A dermoscopic image of a skin lesion.
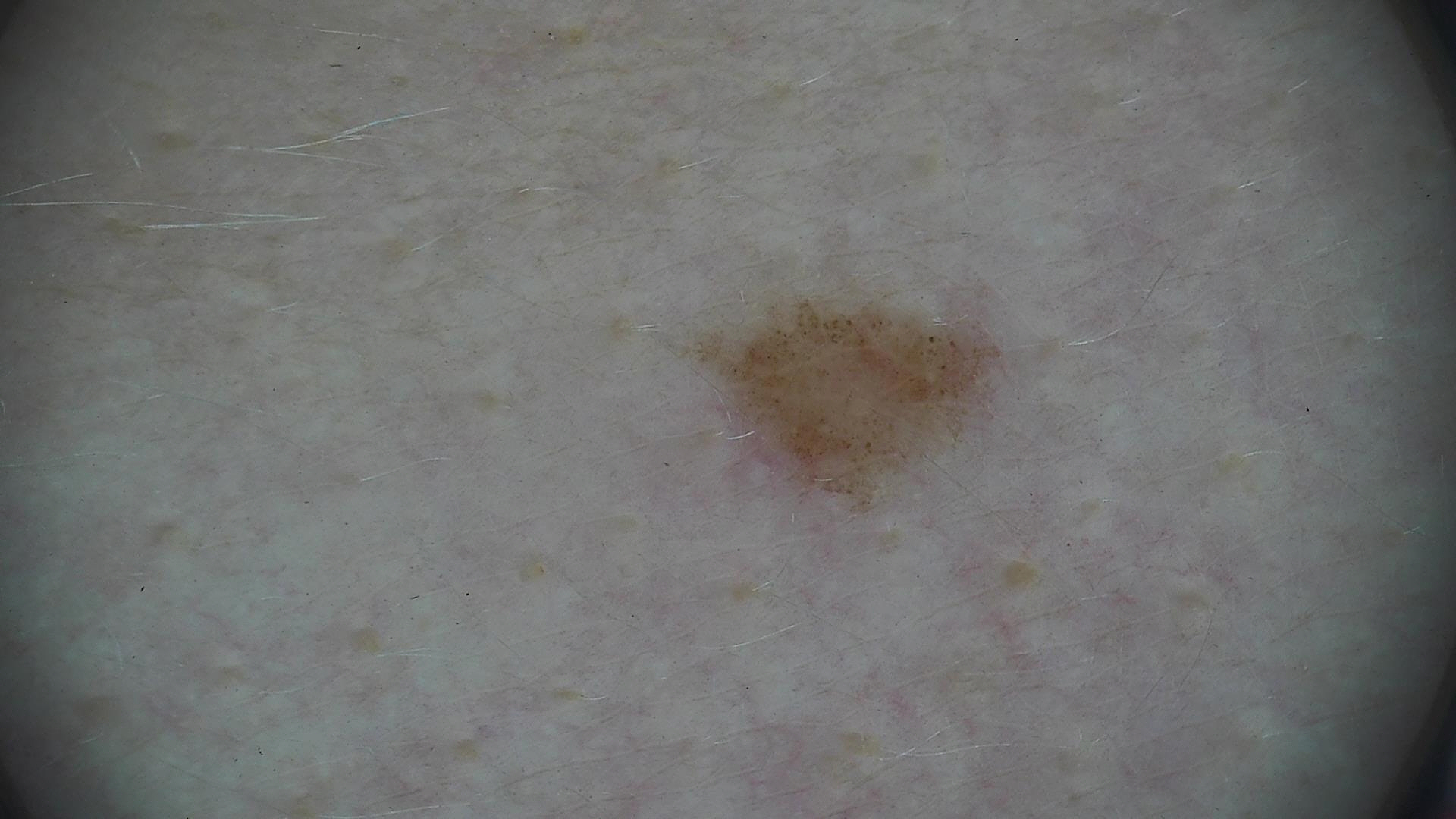assessment: dysplastic junctional nevus (expert consensus).